Dermoscopy of a skin lesion: 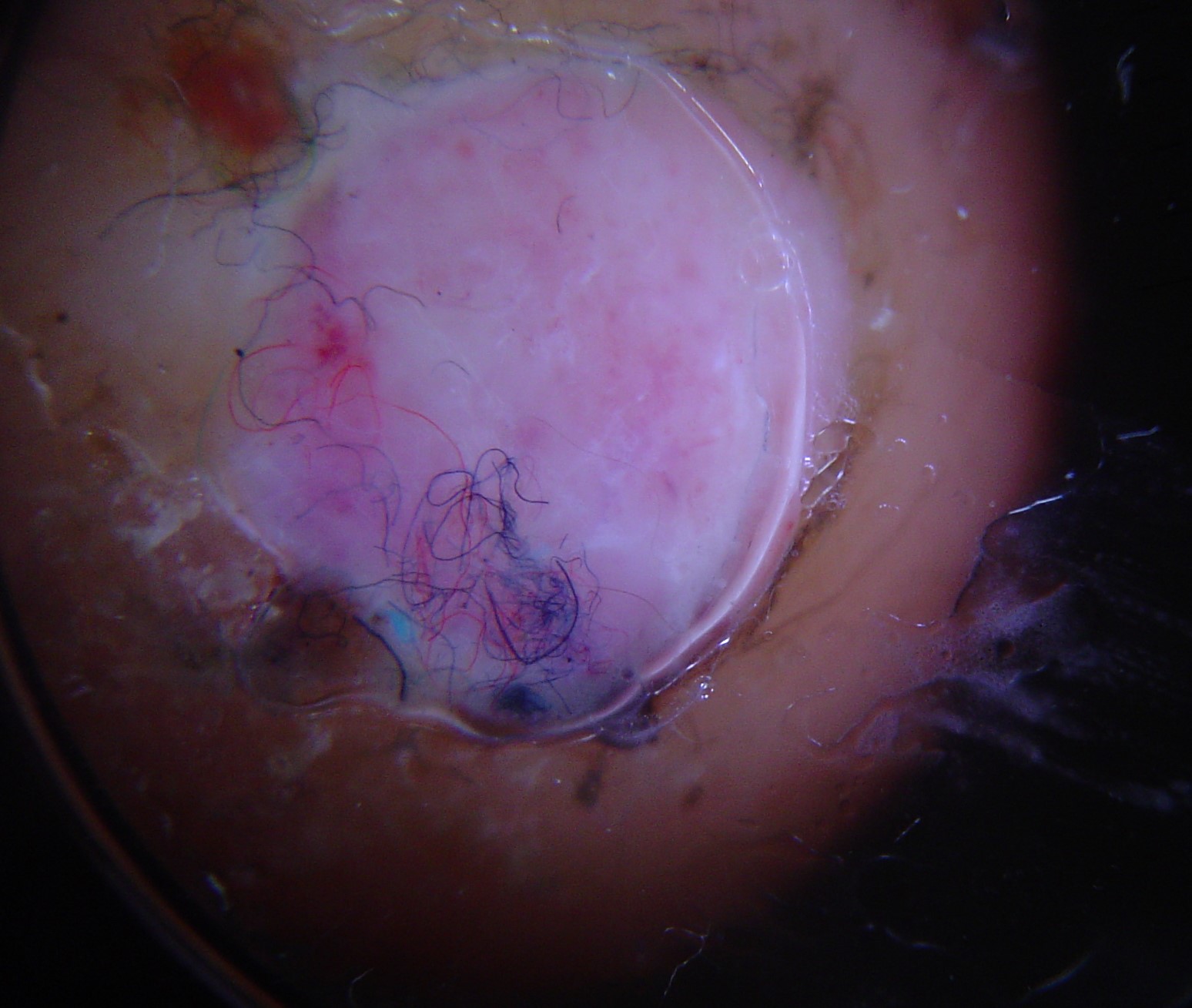Diagnosis: Biopsy-confirmed as a skin cancer — an acral nodular melanoma.